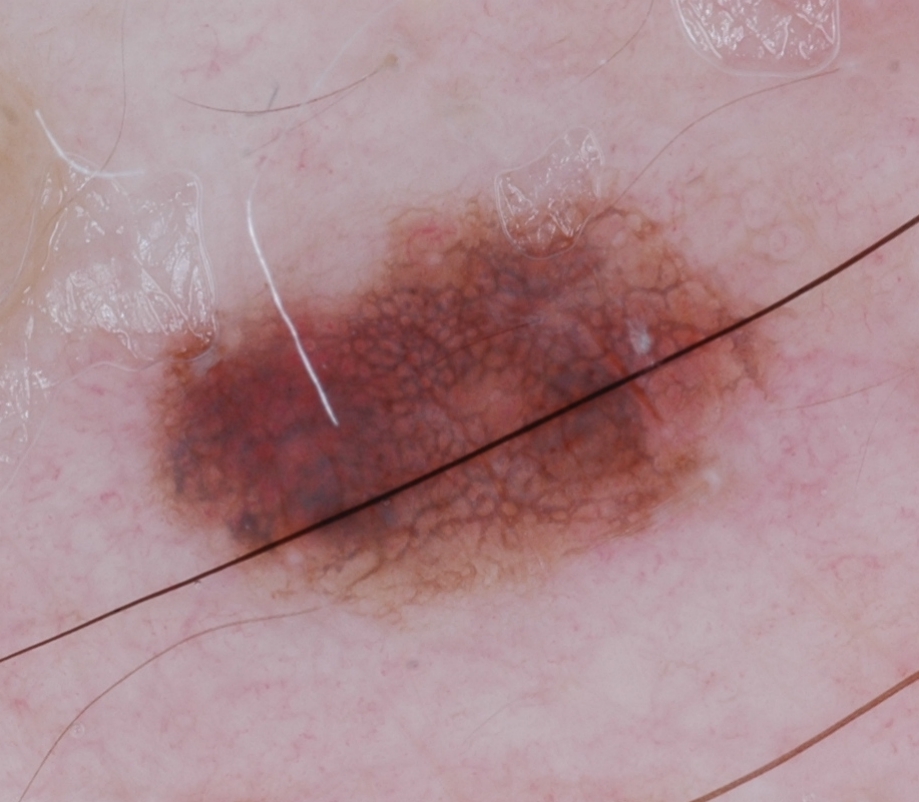A dermatoscopic image of a skin lesion. Dermoscopically, the lesion shows pigment network. Lesion location: <box>134, 180, 815, 637</box>. The lesion was assessed as a melanocytic nevus.